Present for since childhood; the patient also reports fatigue; the patient is female; the photograph was taken at a distance; symptoms reported: bleeding, bothersome appearance, itching and pain — 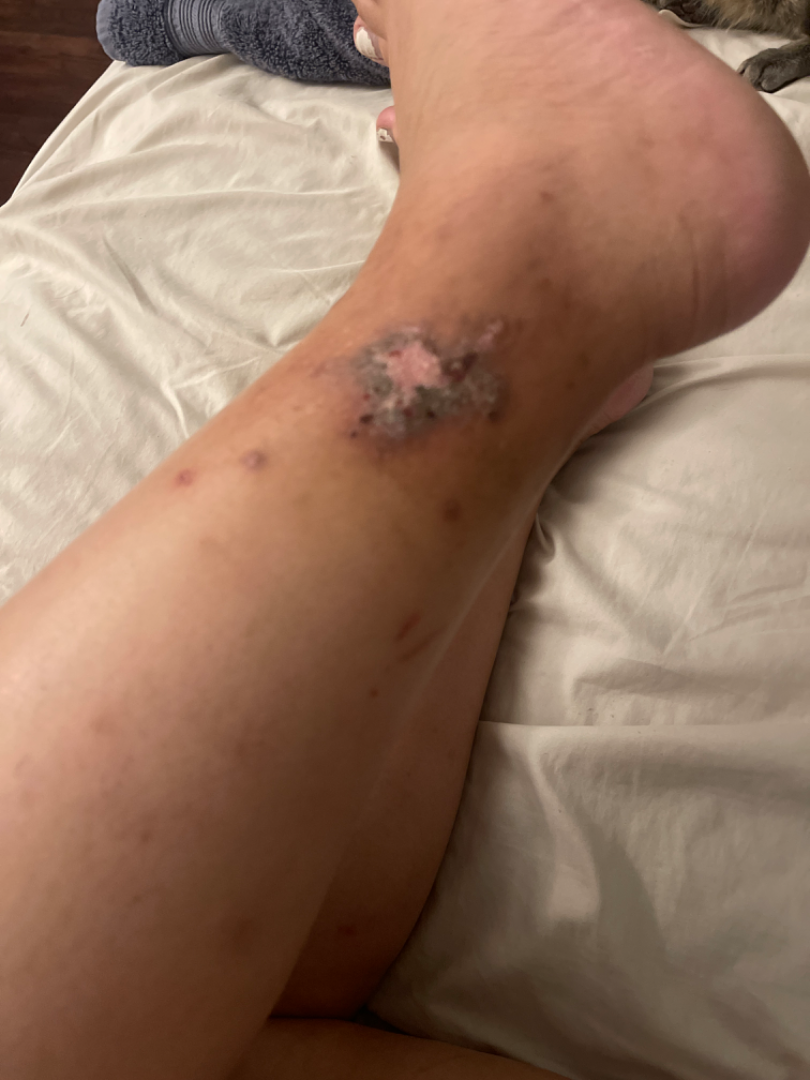{"differential": {"leading": ["Lichen Simplex Chronicus"], "considered": ["Deep fungal infection"], "unlikely": ["SCC/SCCIS"]}}